A close-up photograph · the affected area is the top or side of the foot · self-reported Fitzpatrick phototype V · the patient is a female aged 40–49.
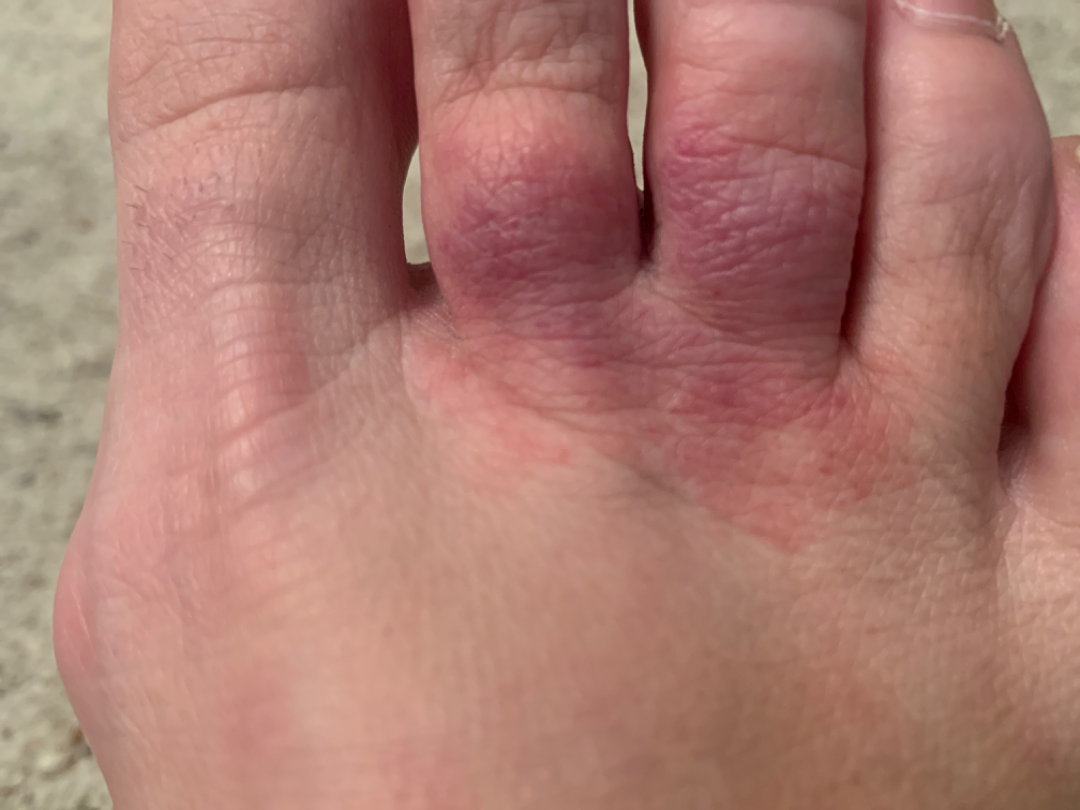One reviewing dermatologist: the impression was split between Acute and chronic dermatitis and Allergic Contact Dermatitis.